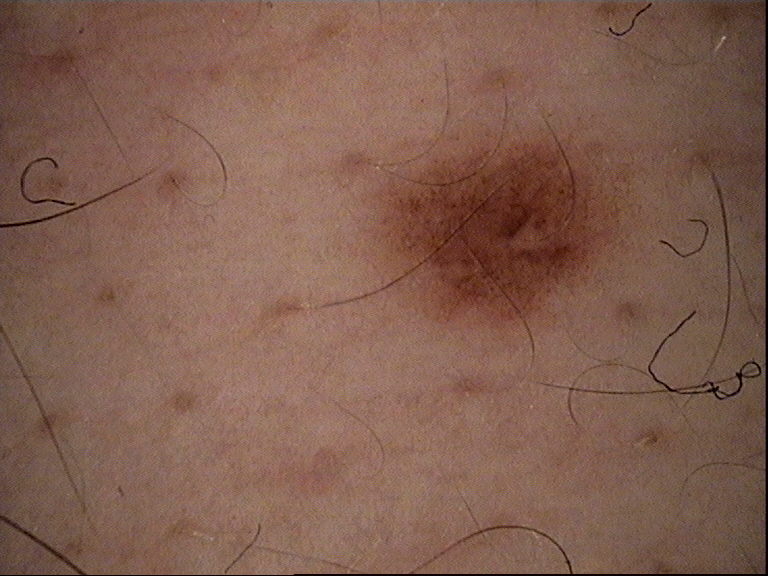class = dysplastic junctional nevus (expert consensus)